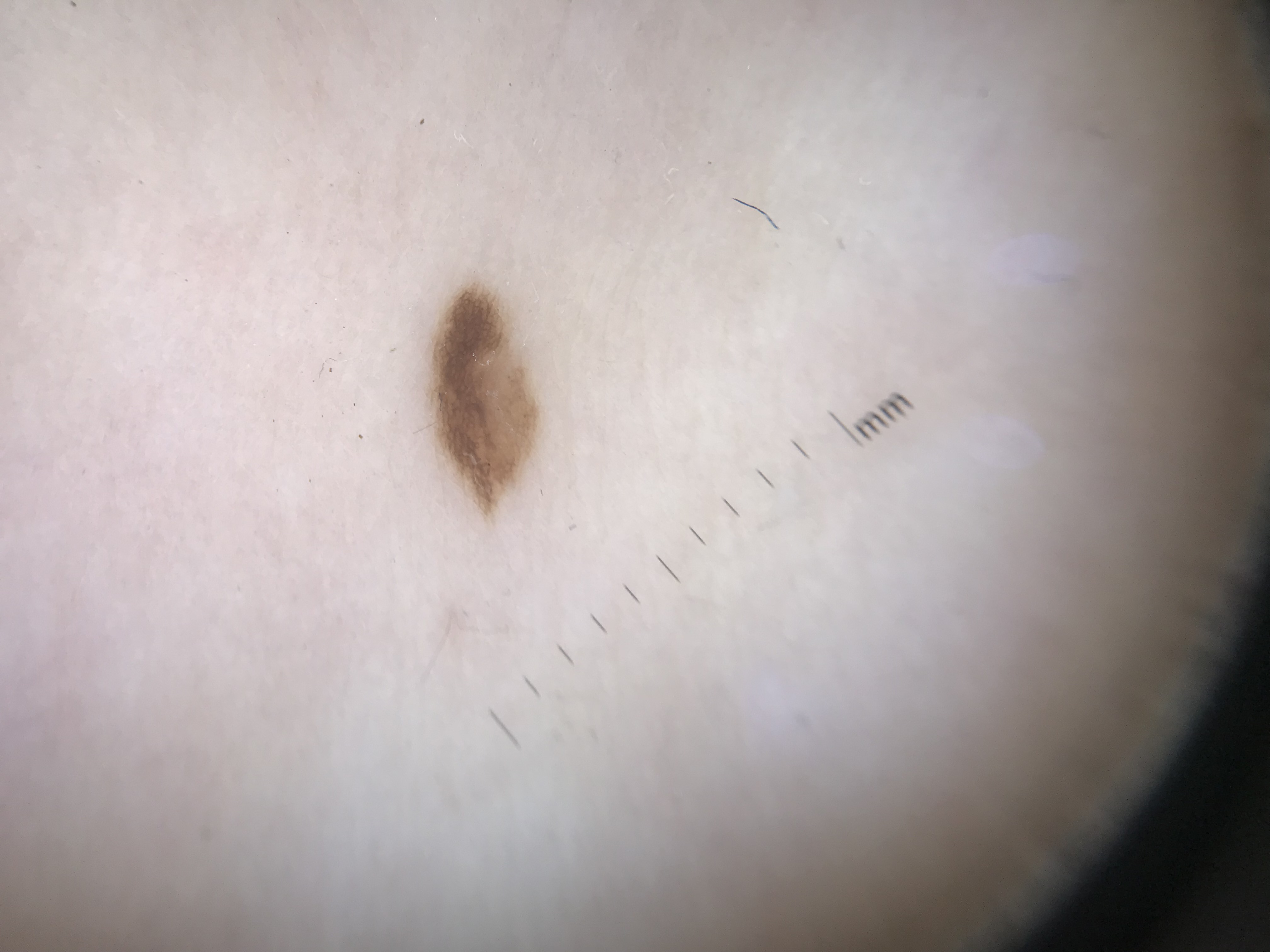A skin lesion imaged with a dermatoscope.
Consistent with a benign lesion — a dysplastic junctional nevus.